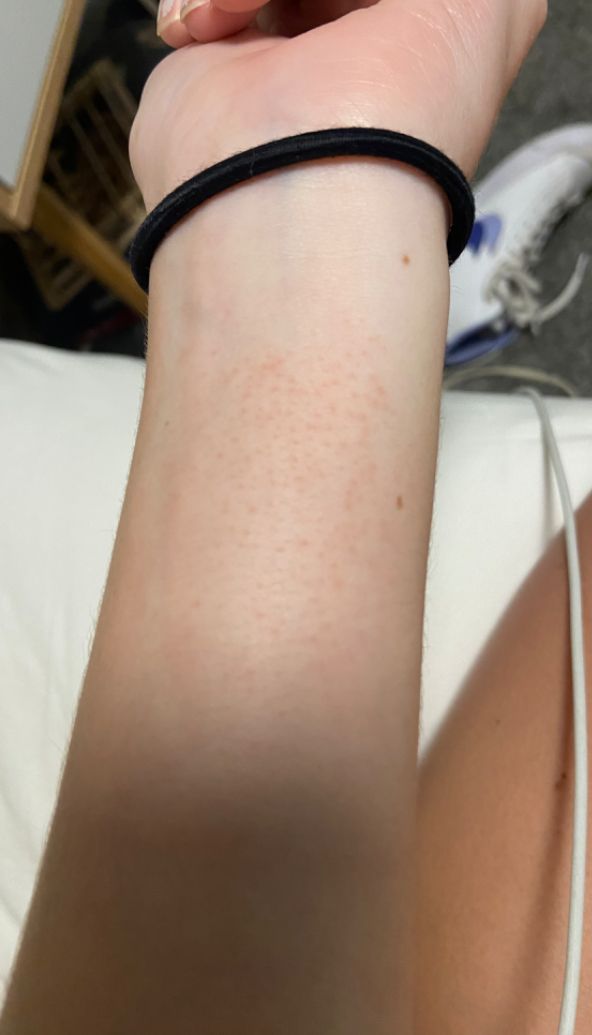assessment: ungradable on photographic review | constitutional symptoms: none reported | image framing: close-up | present for: about one day | surface texture: raised or bumpy | patient's own categorization: a rash | contributor: female | skin tone: non-clinician graders estimated Monk Skin Tone 2 or 3 | anatomic site: arm.